Present for more than one year. The patient reports associated fatigue and joint pain. The lesion is described as raised or bumpy and rough or flaky. The affected area is the back of the hand. Male patient, age 60–69. The lesion is associated with enlargement and bothersome appearance. The photo was captured at a distance. Human graders estimated MST 1 (US pool) or 2 (India pool).
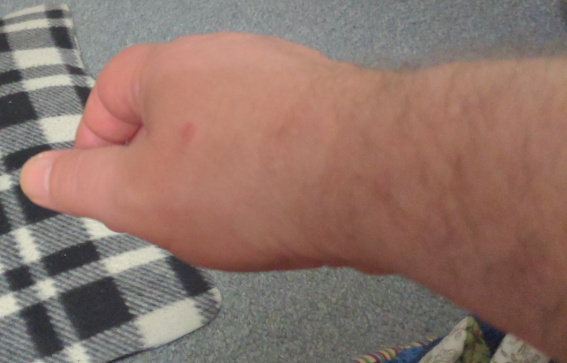Review:
Eczema (0.33); Insect Bite (0.33); Herpes Simplex (0.33).